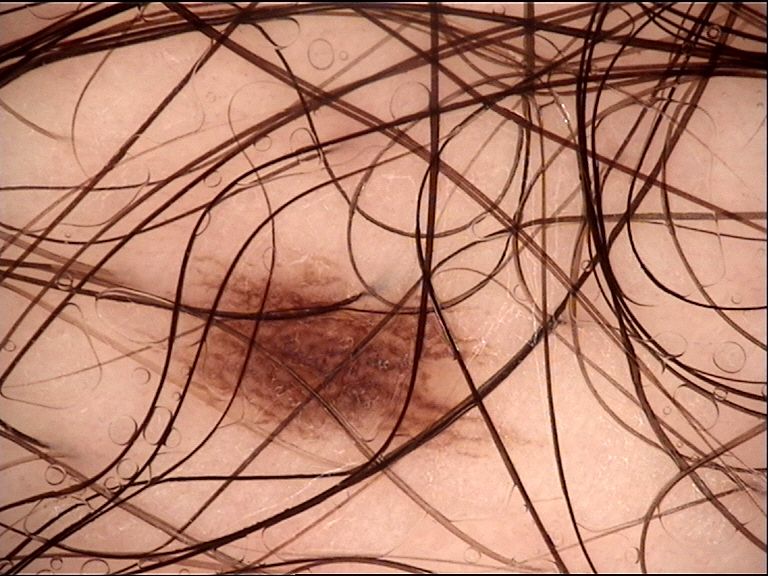A dermoscopic close-up of a skin lesion. The diagnostic label was a benign lesion — a dysplastic junctional nevus.